A clinical photograph of a skin lesion · a patient 53 years old.
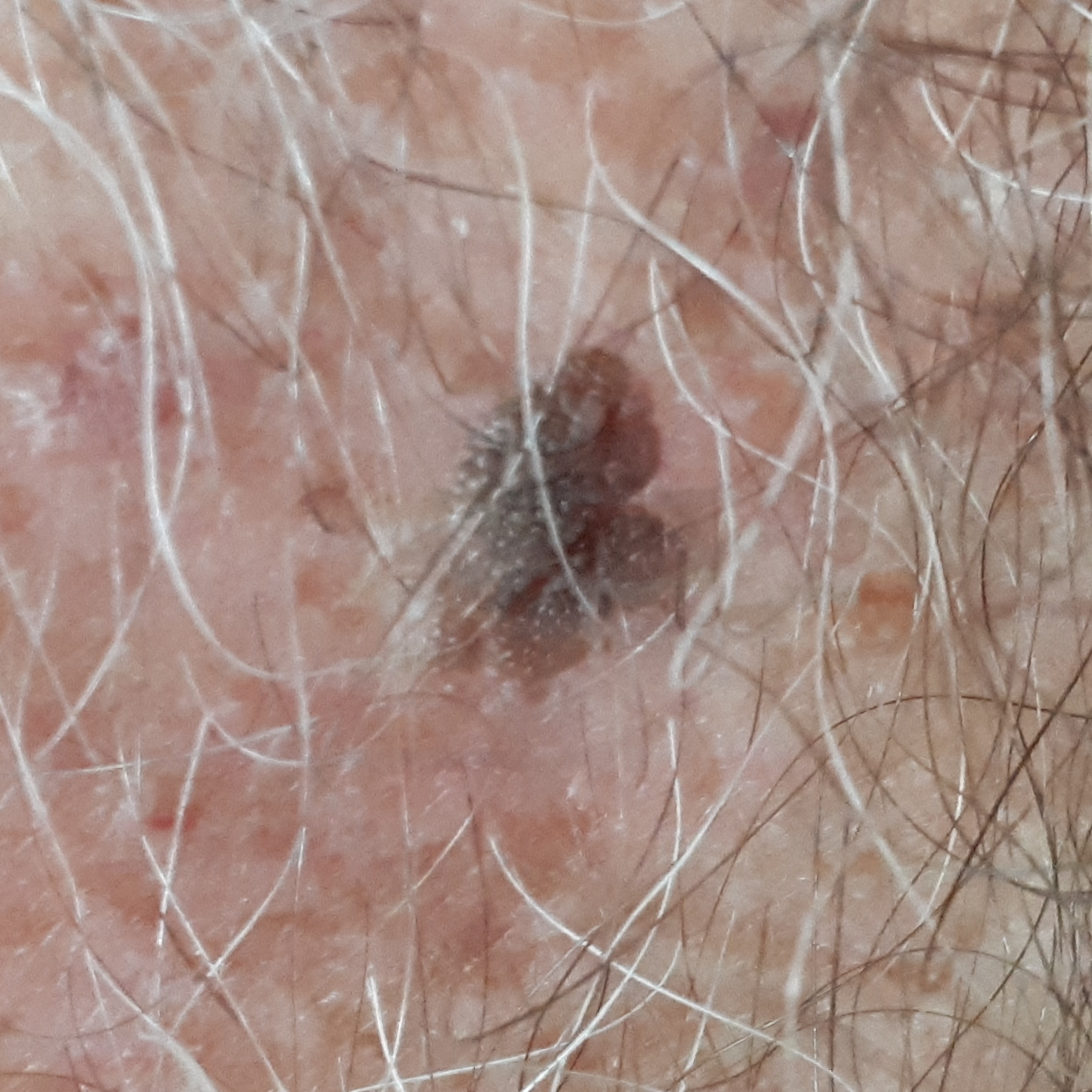Findings:
- body site · the chest
- reported symptoms · elevation / no change in appearance
- diagnosis · seborrheic keratosis (clinical consensus)